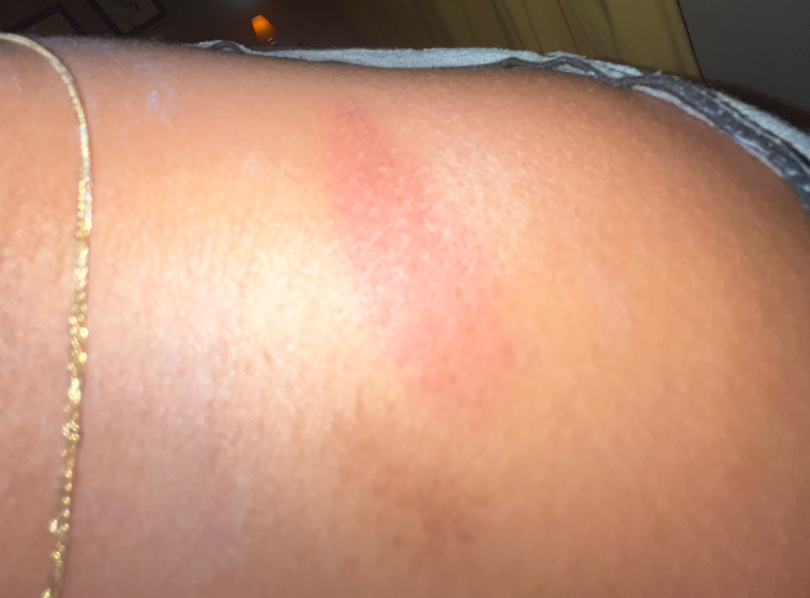Notes:
- assessment — ungradable on photographic review
- body site — head or neck
- image framing — at an angle
- symptom duration — about one day
- other reported symptoms — none reported
- surface texture — raised or bumpy
- patient describes the issue as — a rash